The patient is a female aged 18–29, the patient described the issue as a rash, this image was taken at an angle, reported duration is less than one week, the lesion involves the arm, no associated systemic symptoms reported, symptoms reported: enlargement and itching:
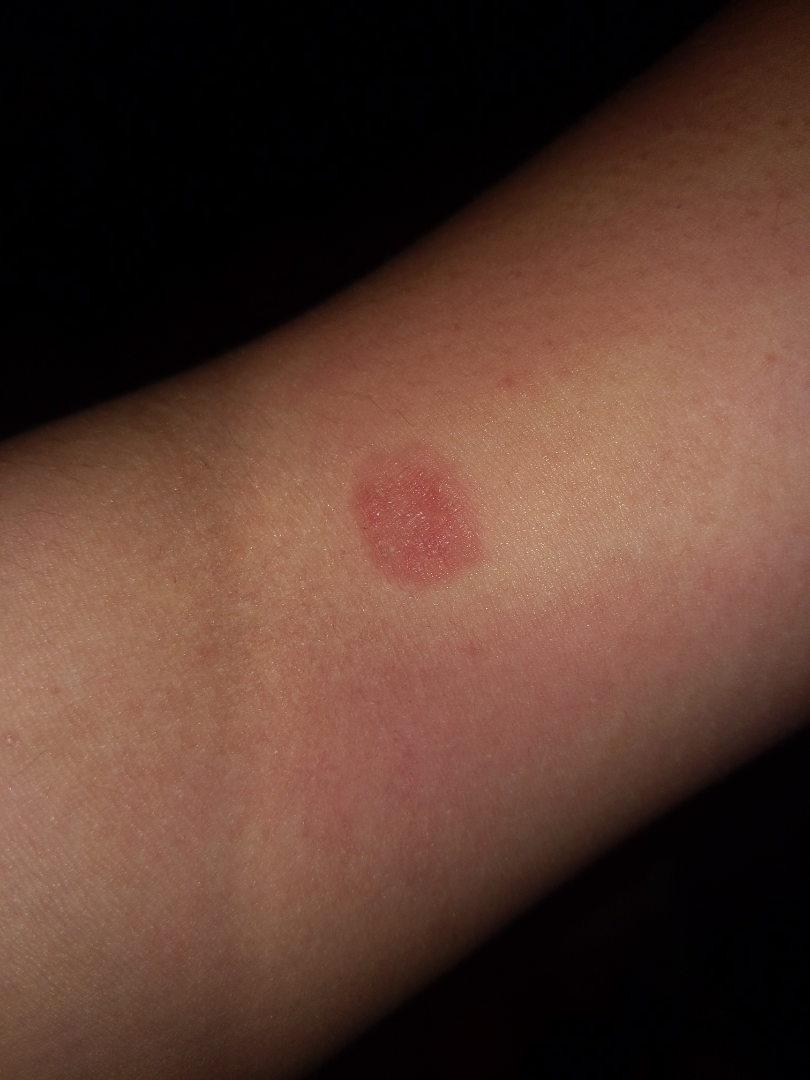On dermatologist assessment of the image, the favored diagnosis is Eczema.